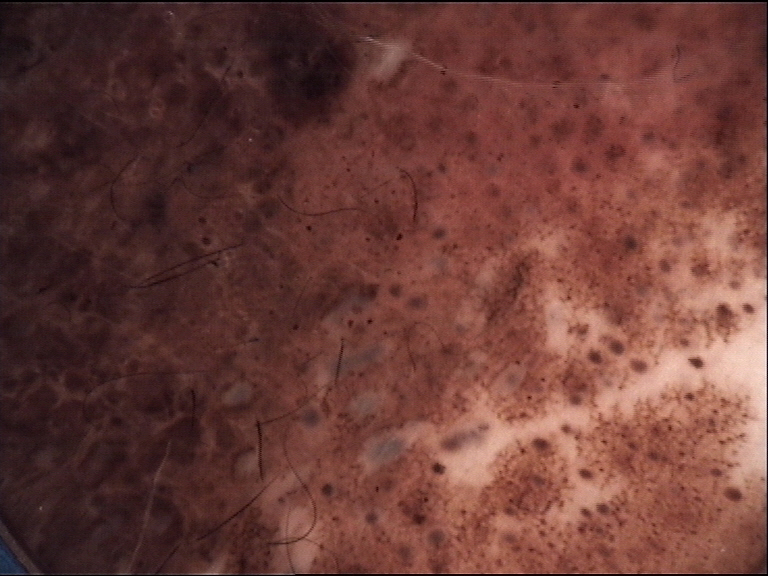  lesion_type:
    main_class: banal
    pattern: compound
  diagnosis:
    name: congenital compound nevus
    code: ccb
    malignancy: benign
    super_class: melanocytic
    confirmation: expert consensus